A female patient, roughly 30 years of age; this is a dermoscopic photograph of a skin lesion — 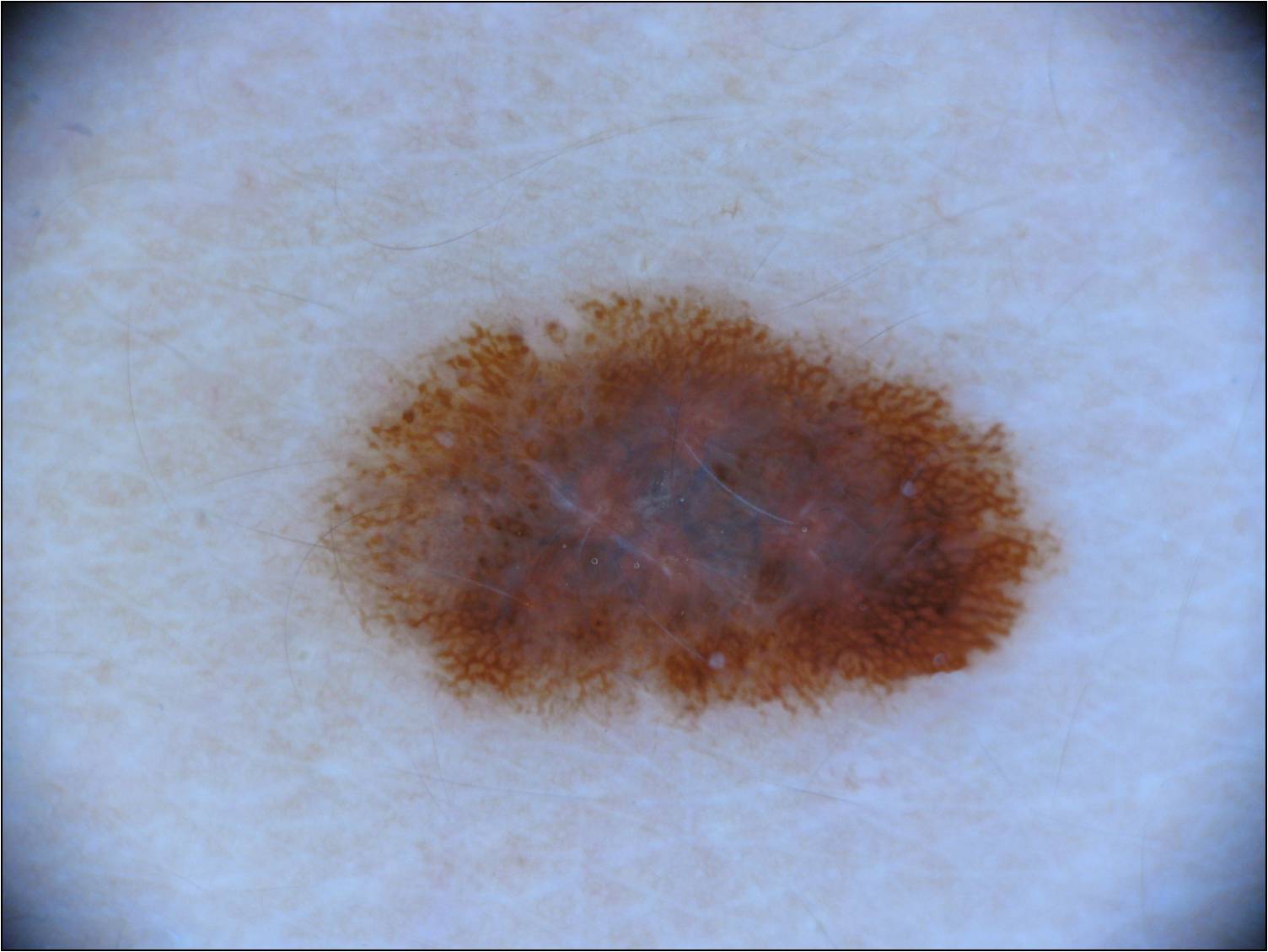dermoscopic_features:
  present:
    - streaks
    - pigment network
    - globules
  absent:
    - milia-like cysts
    - negative network
lesion_location:
  bbox_xyxy:
    - 316
    - 283
    - 1058
    - 729
diagnosis:
  name: melanocytic nevus
  malignancy: benign
  lineage: melanocytic
  provenance: clinical